This is a close-up image · the head or neck and arm are involved: 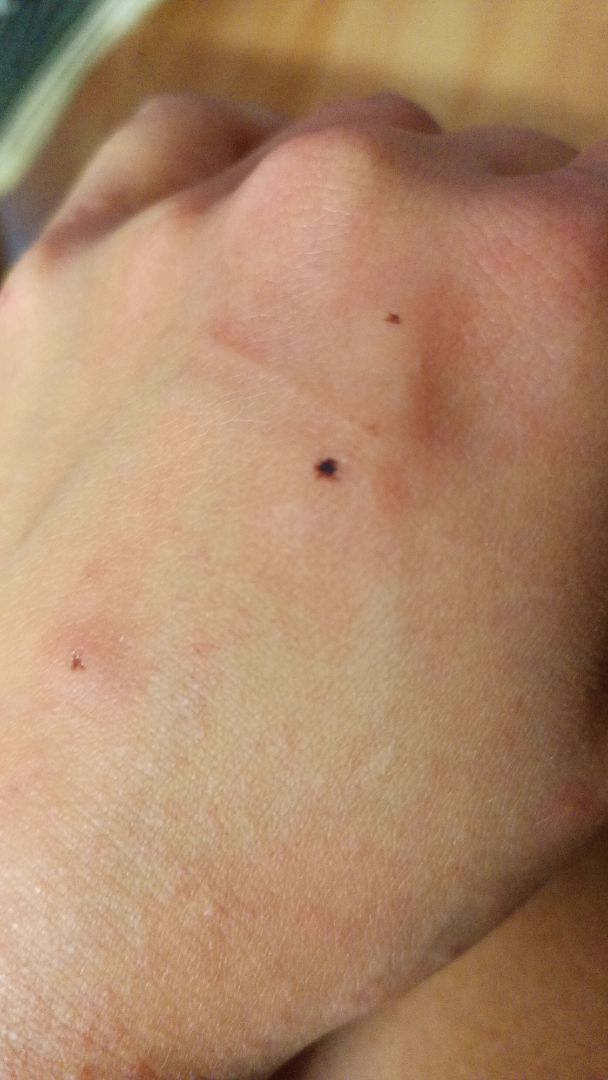The skin findings could not be characterized from the image.